A dermatoscopic image of a skin lesion.
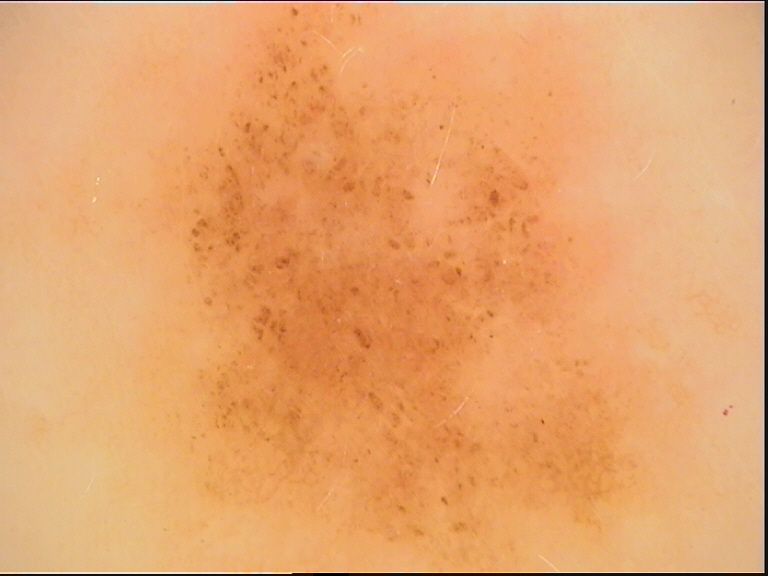diagnosis = dysplastic junctional nevus (expert consensus).